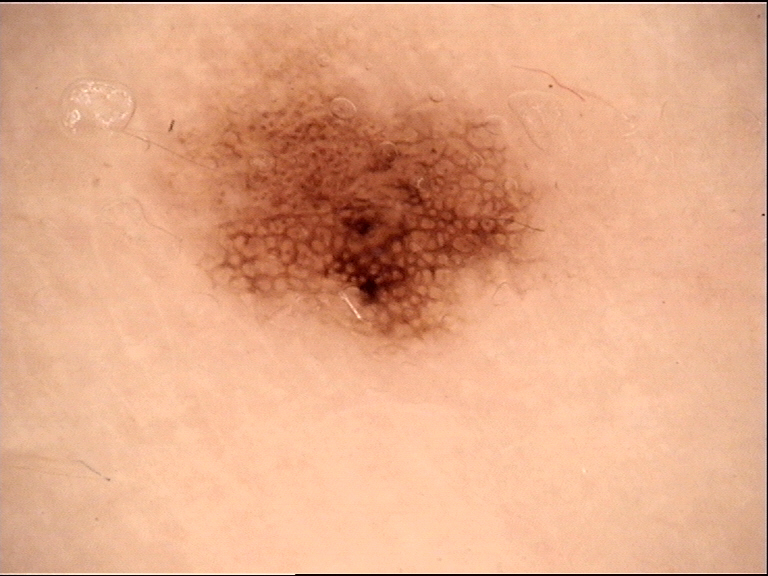diagnostic label — dysplastic junctional nevus (expert consensus).